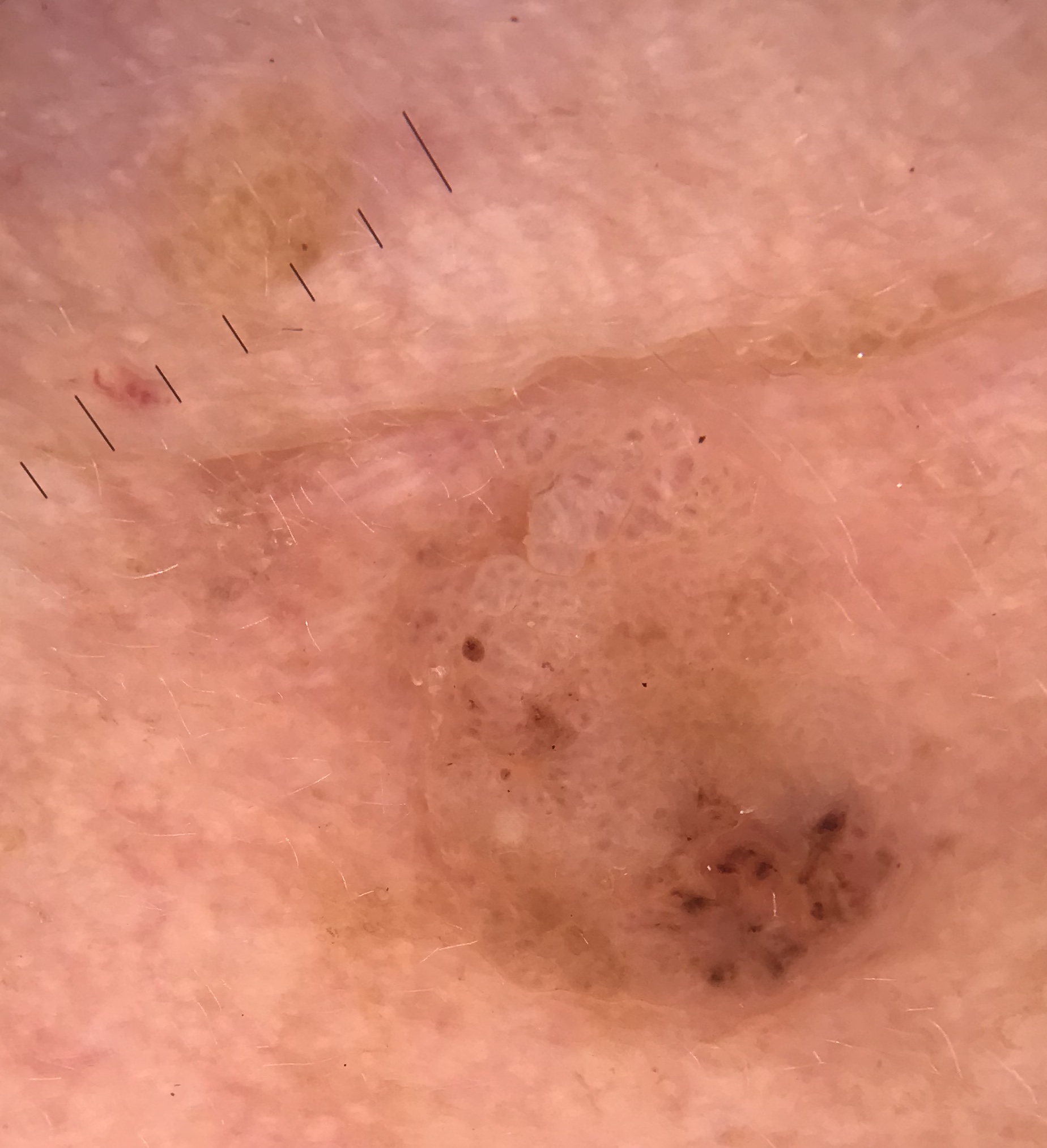A dermoscopic image of a skin lesion. The architecture is that of a keratinocytic lesion. Diagnosed as a benign lesion — a seborrheic keratosis.